A patient in their late 50s · a clinical photograph showing a skin lesion.
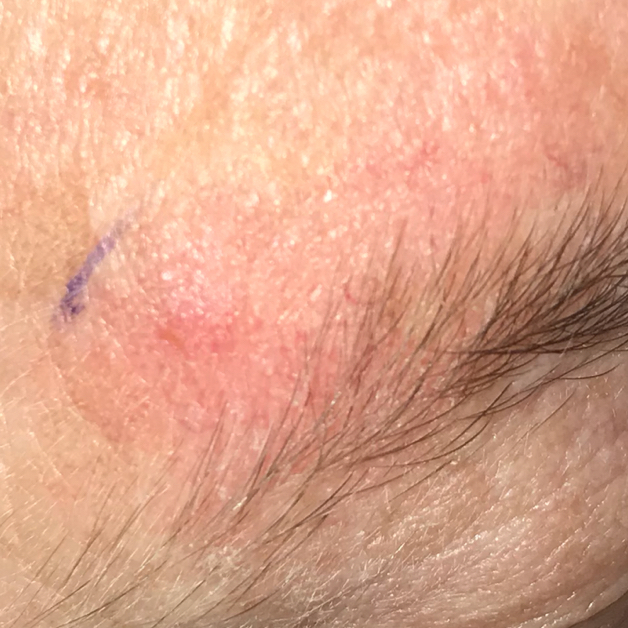The patient reports that the lesion has changed, has grown, and itches, but is not elevated and has not bled.
The diagnostic impression was a lesion with uncertain malignant potential — an actinic keratosis.